A male patient approximately 45 years of age · a dermoscopy image of a single skin lesion: 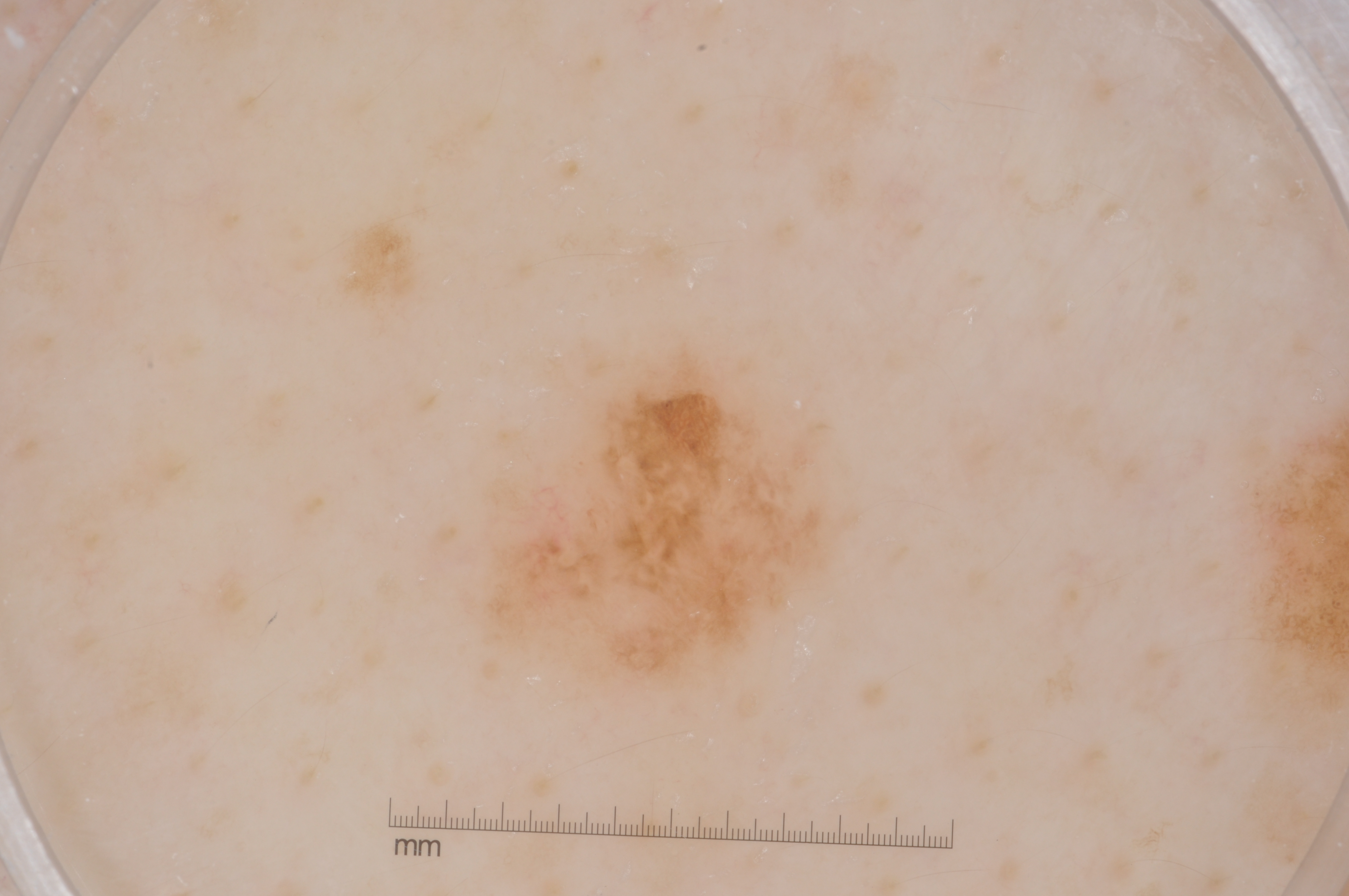Image and clinical context: The lesion spans (495, 357, 843, 686). Dermoscopy demonstrates negative network and pigment network. Impression: Expert review diagnosed this as a melanocytic nevus.